The photograph is a close-up of the affected area. The patient is 50–59, female. No associated systemic symptoms reported. The patient reports darkening, itching, bothersome appearance, burning and pain. Self-reported Fitzpatrick phototype III; lay reviewers estimated 2 on the MST. The condition has been present for three to twelve months. The patient reports the lesion is raised or bumpy.
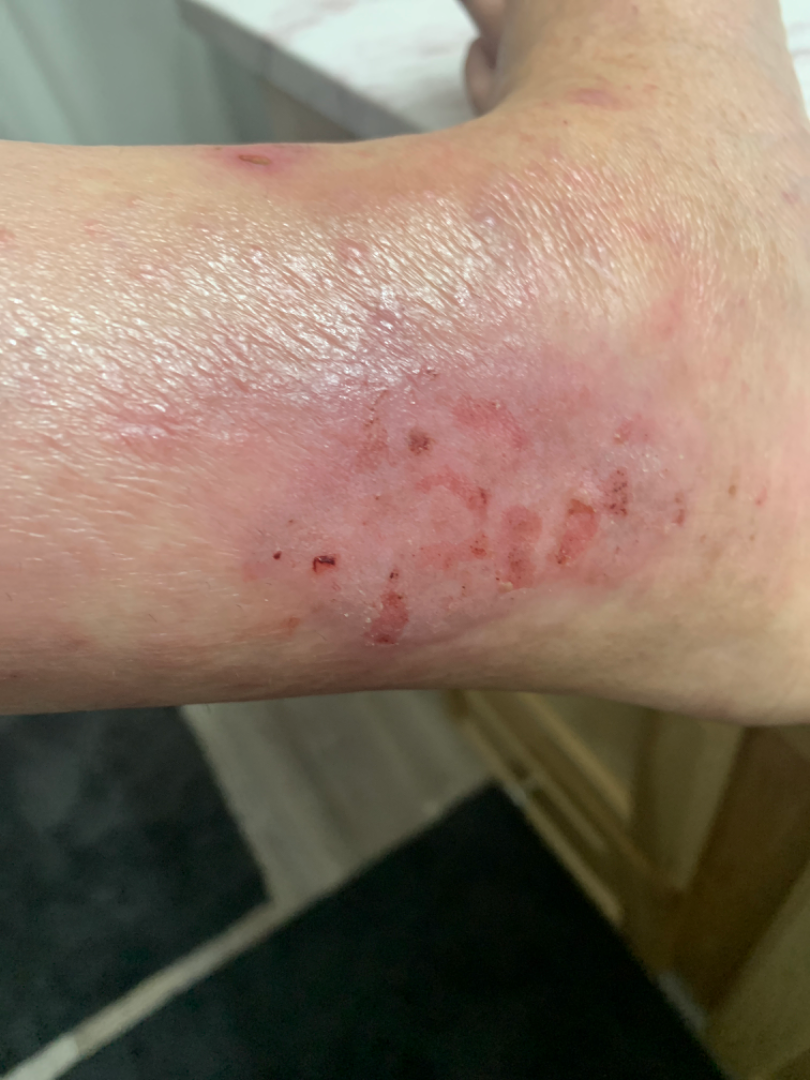The case was indeterminate on photographic review.